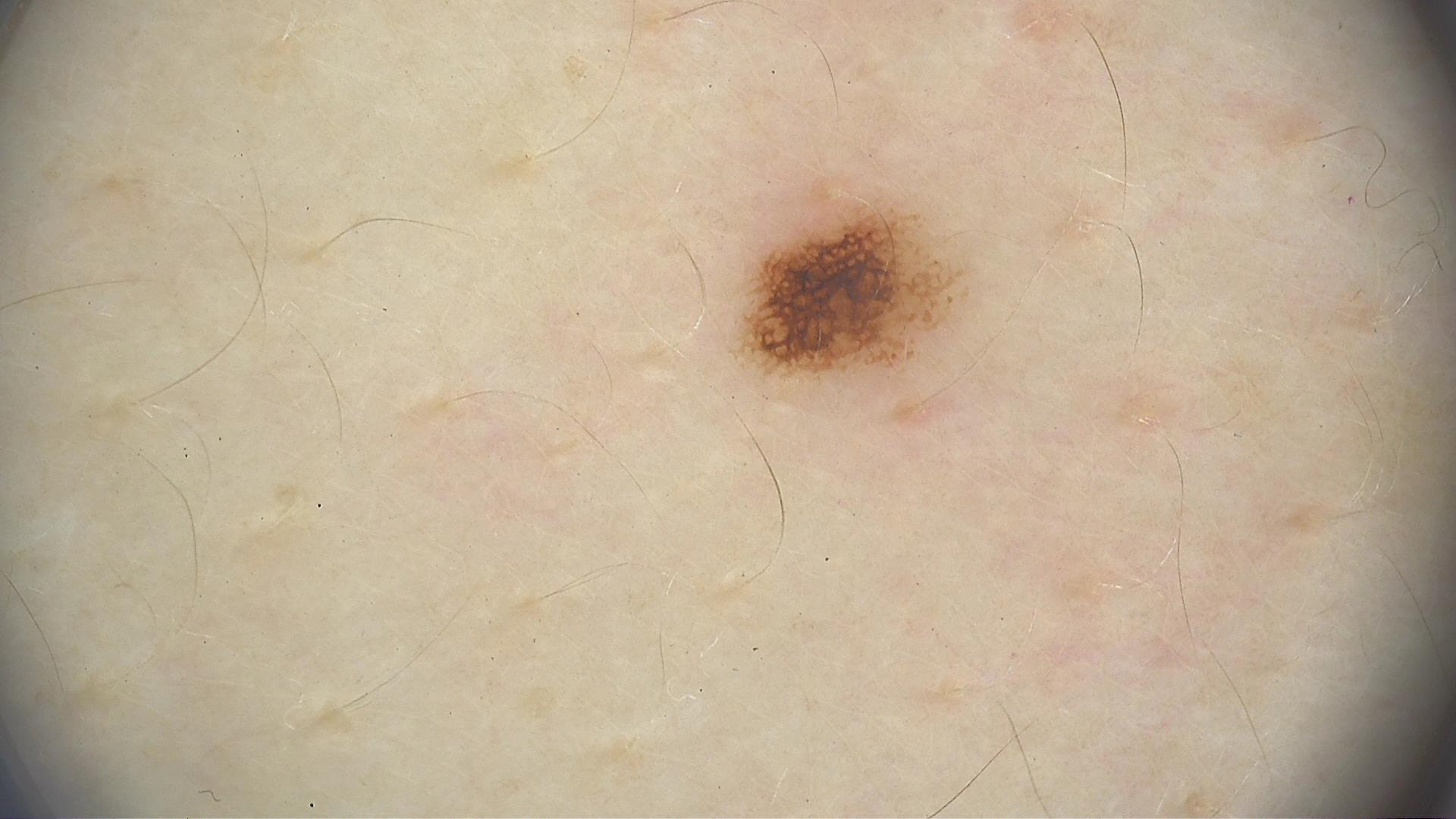| key | value |
|---|---|
| image | dermoscopy |
| label | dysplastic junctional nevus (expert consensus) |